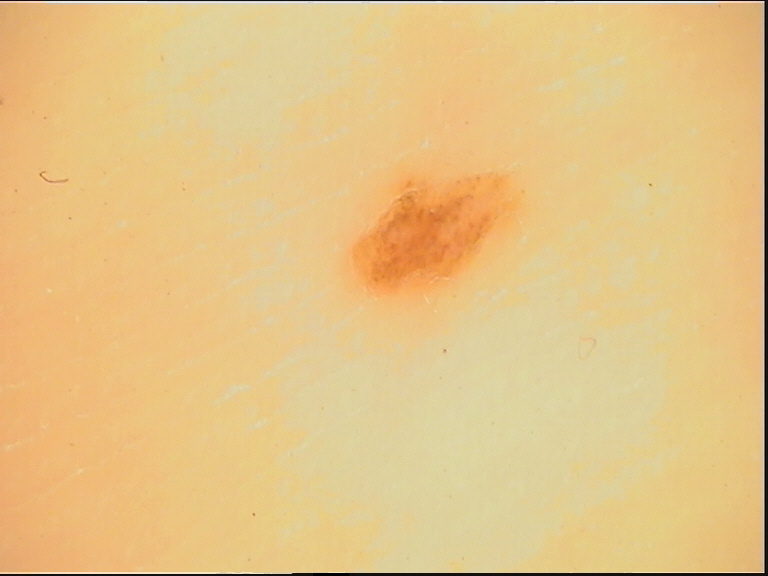Q: What is the imaging modality?
A: dermoscopy
Q: What is this lesion?
A: acral dysplastic junctional nevus (expert consensus)